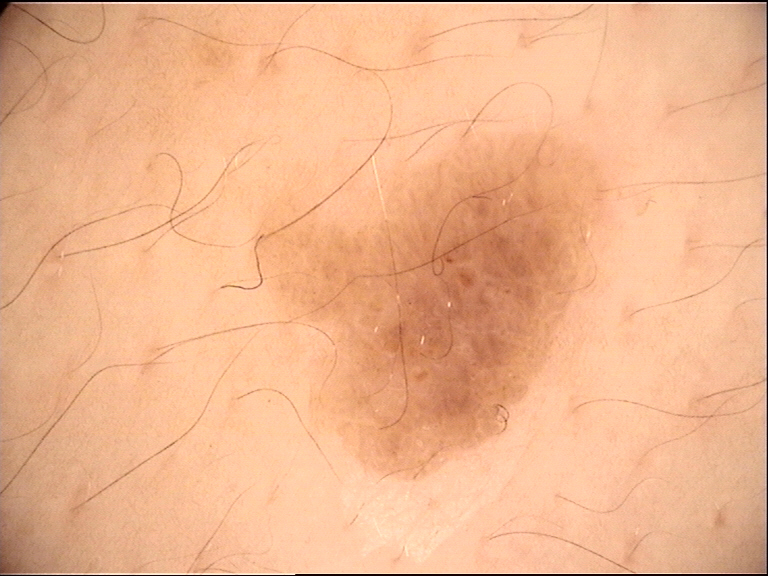A dermoscopic close-up of a skin lesion. This is a keratinocytic lesion. The diagnostic label was a benign lesion — a seborrheic keratosis.